The front of the torso and leg are involved; the photograph is a close-up of the affected area; the subject is a female aged 18–29:
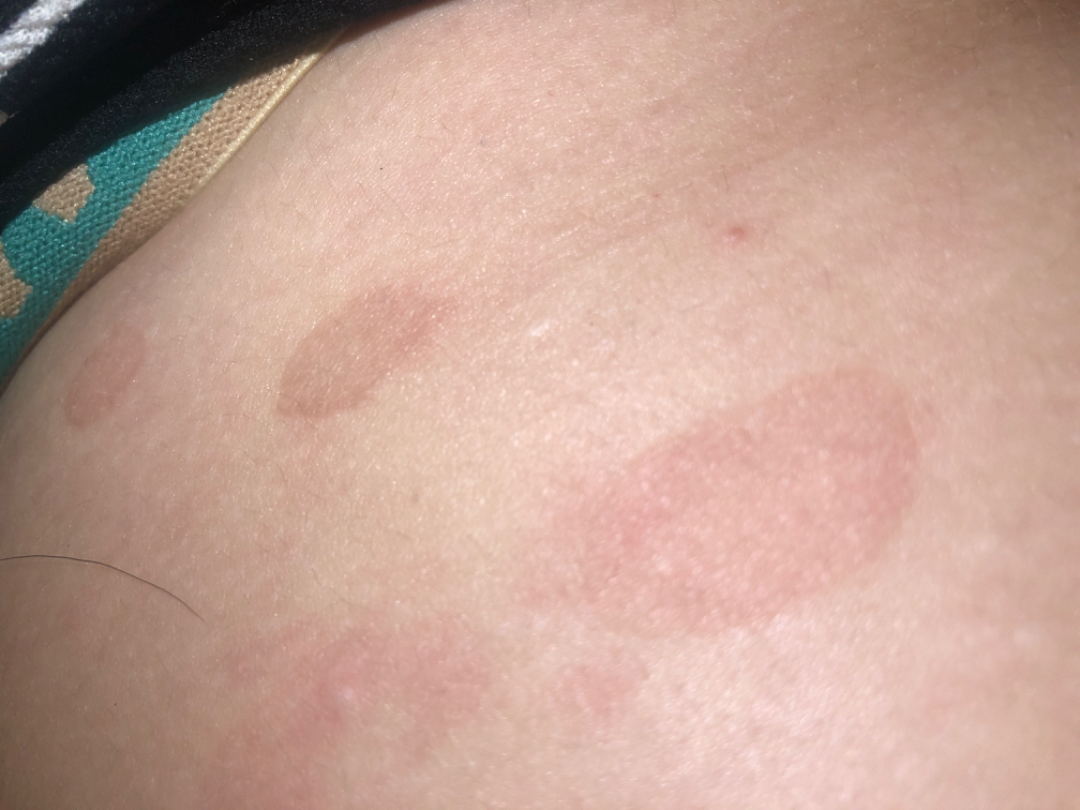On photographic review by a dermatologist: the impression was split between Parapsoriasis, Syphilis and Seborrheic Dermatitis.